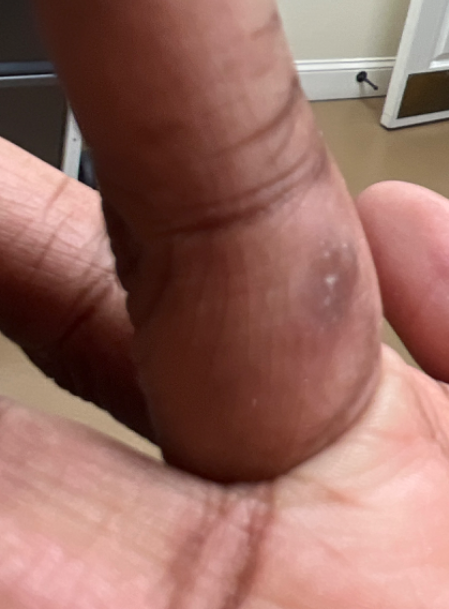photo taken: at an angle
described texture: raised or bumpy, fluid-filled and rough or flaky
patient-reported symptoms: none reported
subject: female, age 18–29
history: less than one week
assessment: favoring Verruca vulgaris